A smartphone photograph of a skin lesion. A patient 47 years of age — 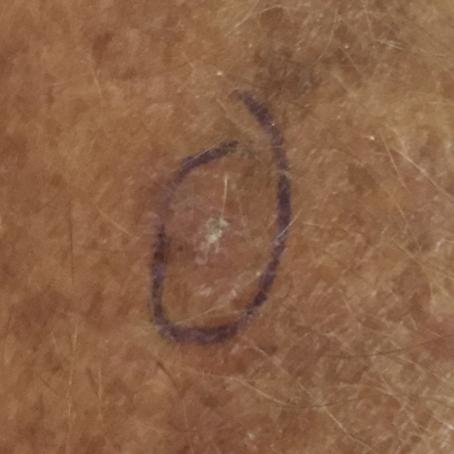{"lesion_location": "a forearm", "symptoms": {"present": ["itching"]}, "diagnosis": {"name": "actinic keratosis", "code": "ACK", "malignancy": "indeterminate", "confirmation": "clinical consensus"}}